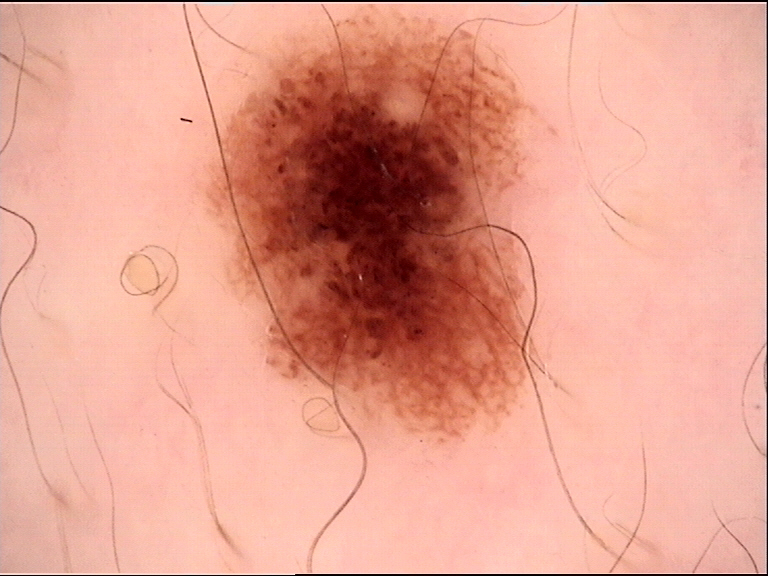A dermatoscopic image of a skin lesion. Consistent with a benign lesion — a dysplastic junctional nevus.